Recorded as skin type II; a clinical photo of a skin lesion taken with a smartphone; a male subject in their 60s; history notes pesticide exposure, tobacco use, alcohol use, and no prior skin cancer (patient or family).
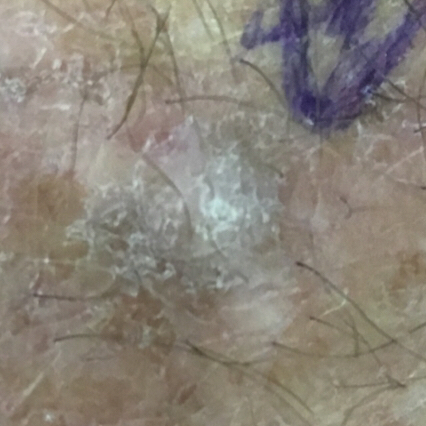The lesion is located on a hand. The lesion is roughly 8 by 7 mm. The patient reports that the lesion is elevated and hurts. Biopsy-confirmed as a skin cancer — a squamous cell carcinoma.